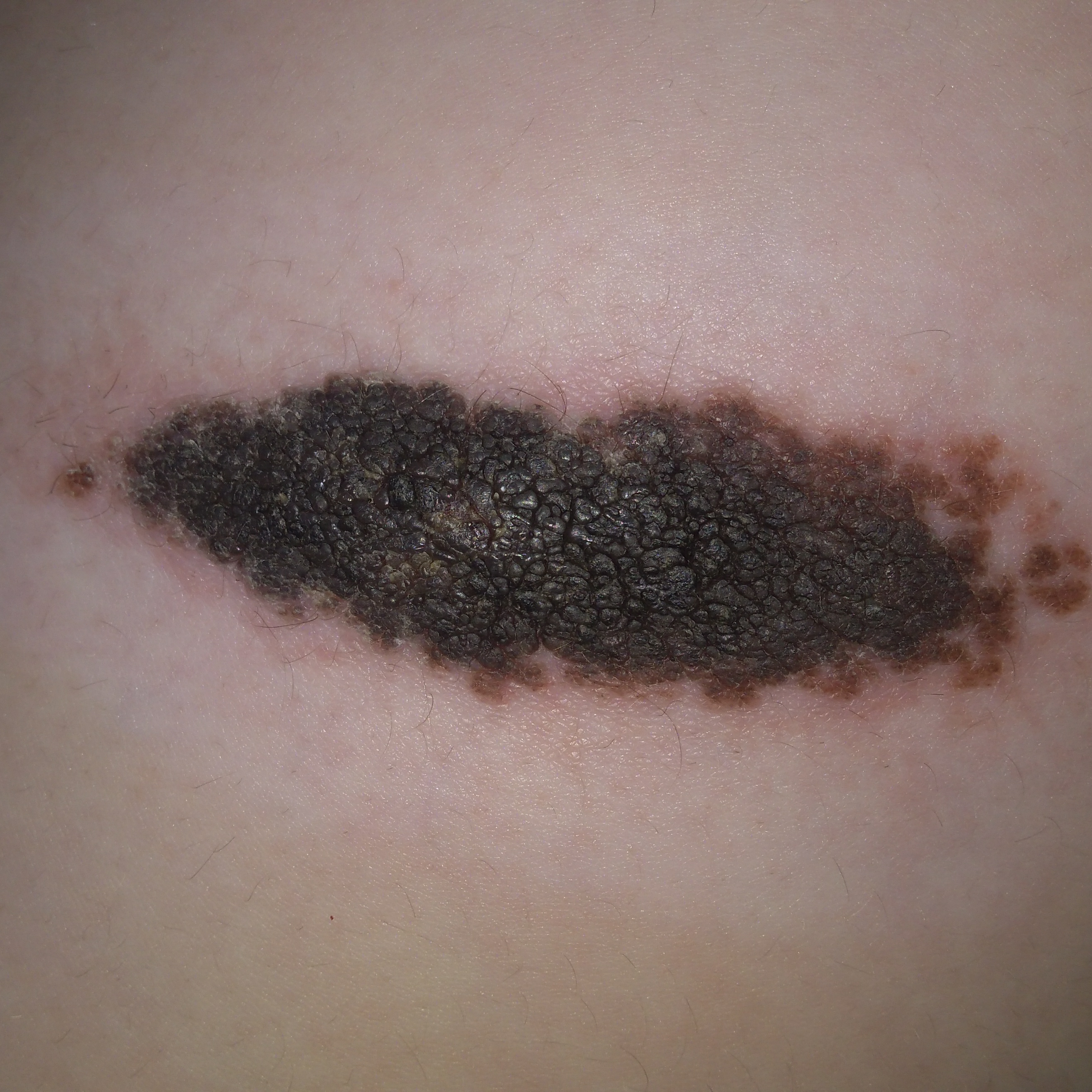Q: Tell me about the patient.
A: female, 13 years old
Q: What kind of image is this?
A: clinical photograph
Q: What is the anatomic site?
A: a thigh
Q: What does the patient describe?
A: elevation / no itching
Q: What is this lesion?
A: nevus (biopsy-proven)